The lesion involves the top or side of the foot, arm, front of the torso, leg and head or neck. An image taken at an angle. The subject is a male aged 18–29: 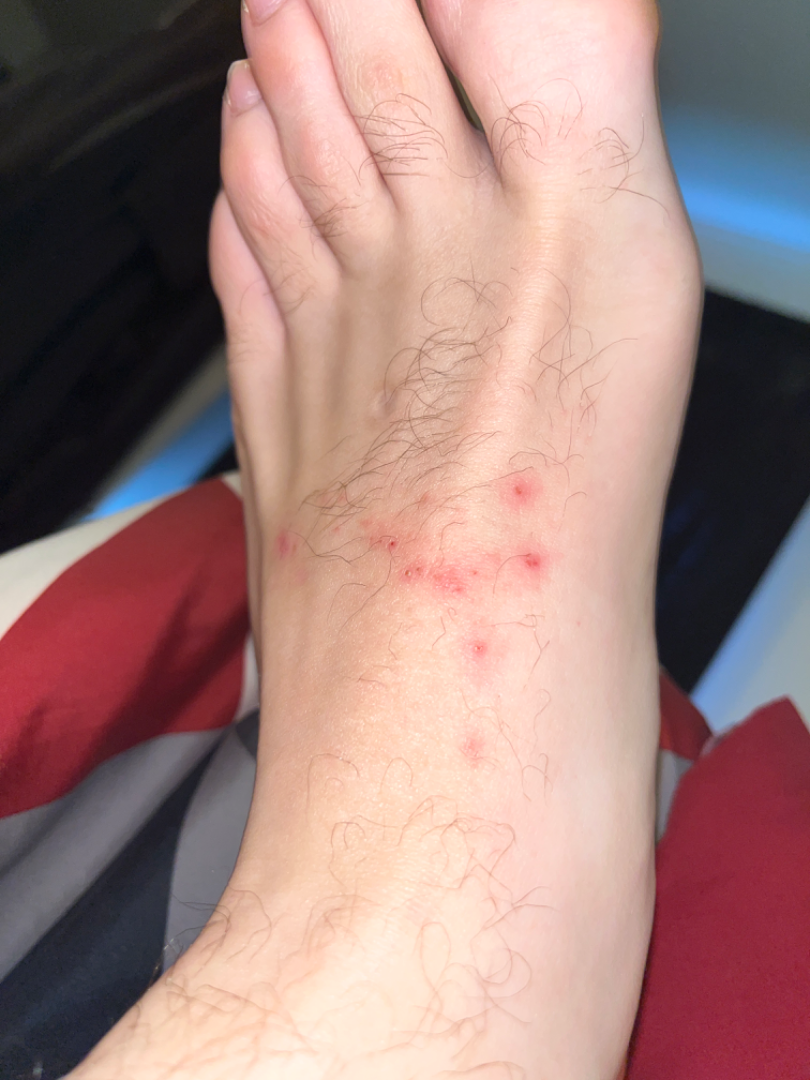{"symptoms": "itching", "differential": {"tied_lead": ["Folliculitis", "Herpes Zoster", "Allergic Contact Dermatitis"]}}